A dermatoscopic image of a skin lesion.
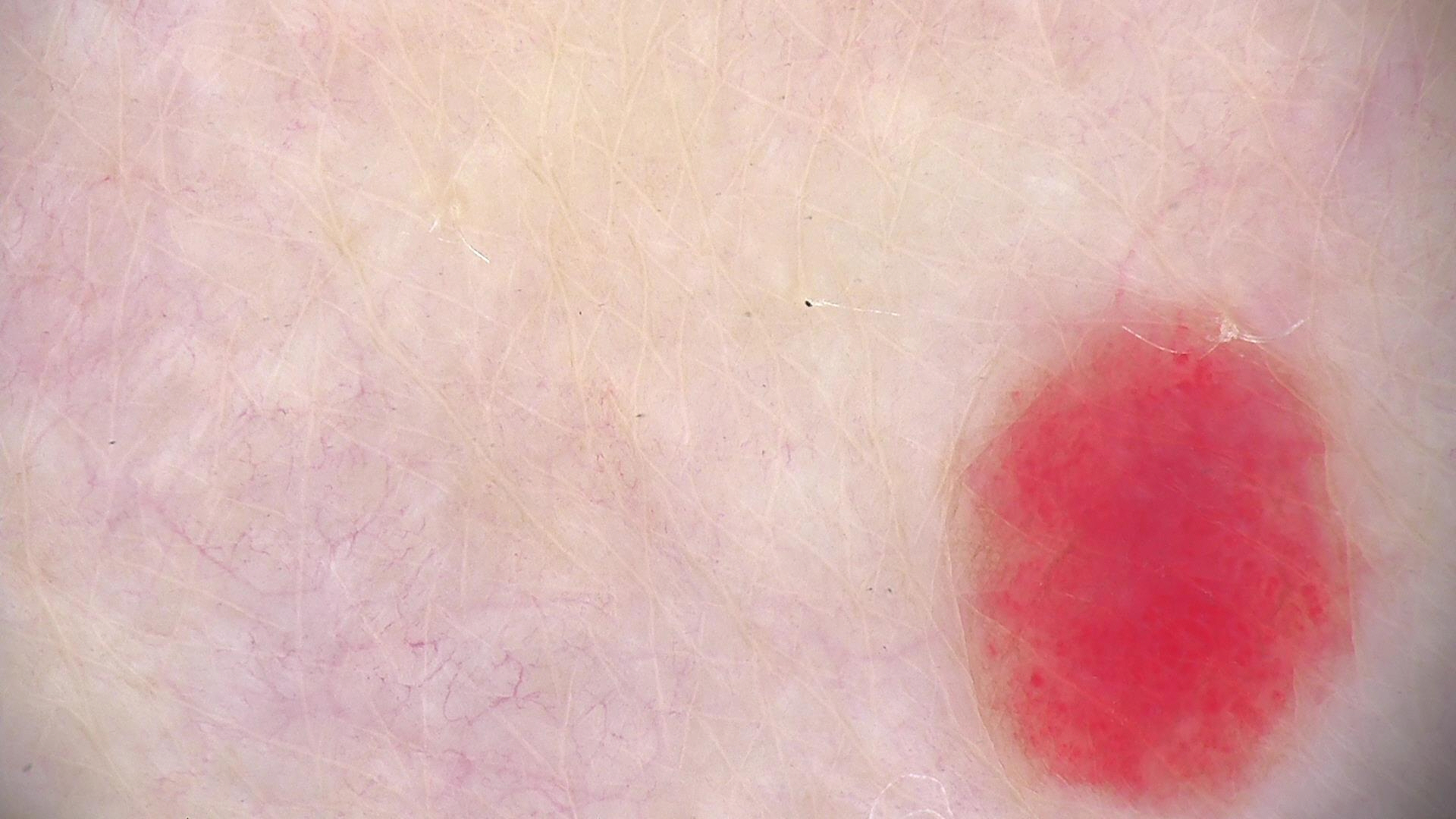Diagnosed as a vascular lesion — a hemangioma.